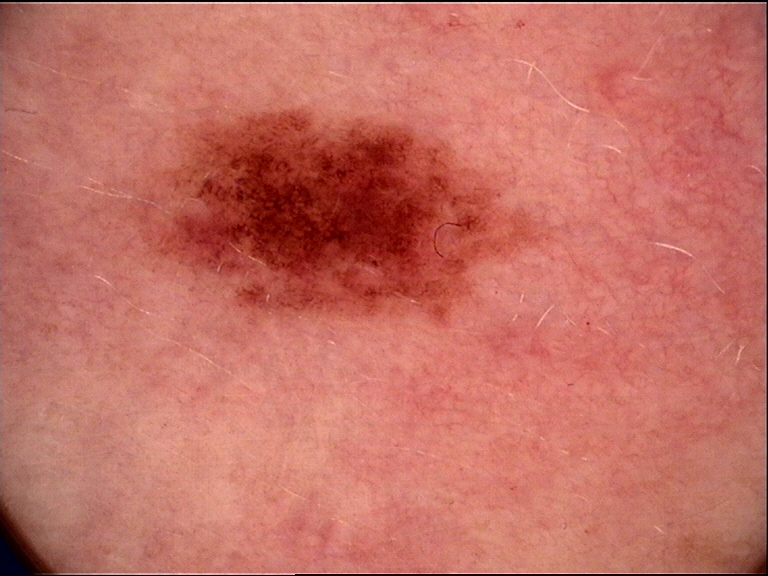Dermoscopy of a skin lesion.
Diagnosed as a dysplastic junctional nevus.